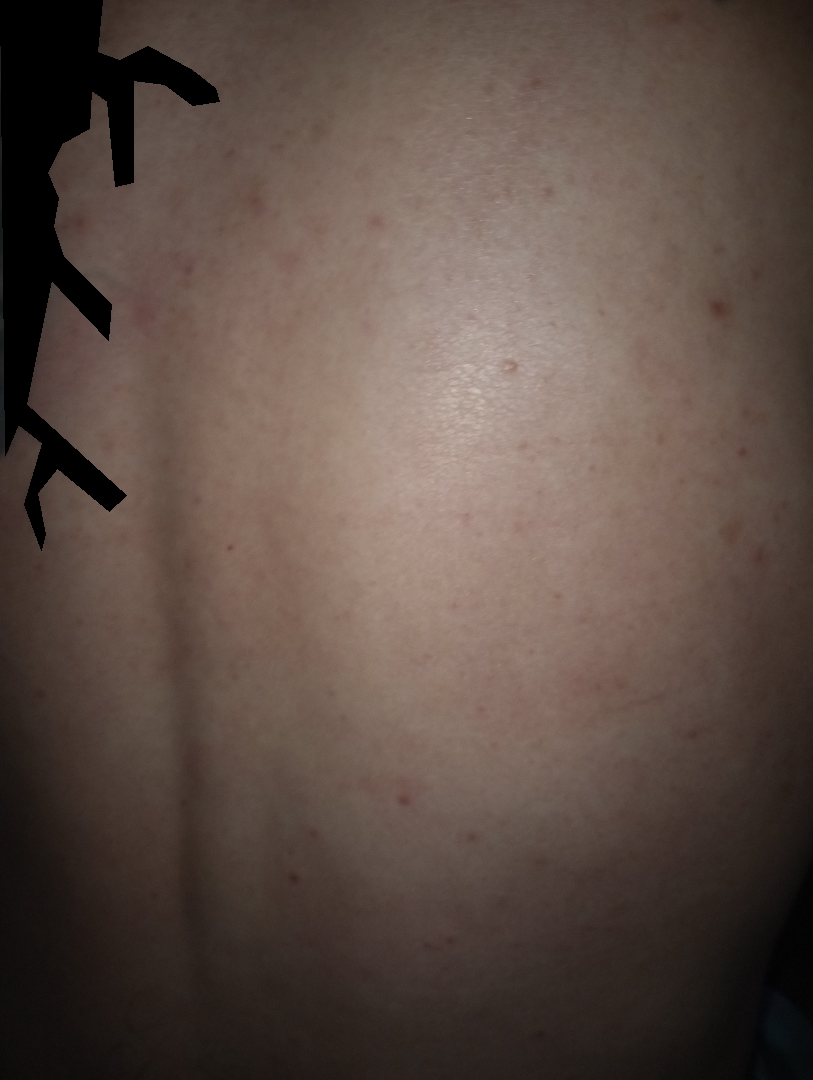Q: Fitzpatrick or Monk tone?
A: FST II
Q: What is the framing?
A: close-up
Q: What is the dermatologist's impression?
A: Acne (41%); Folliculitis (41%); Scabies (18%)